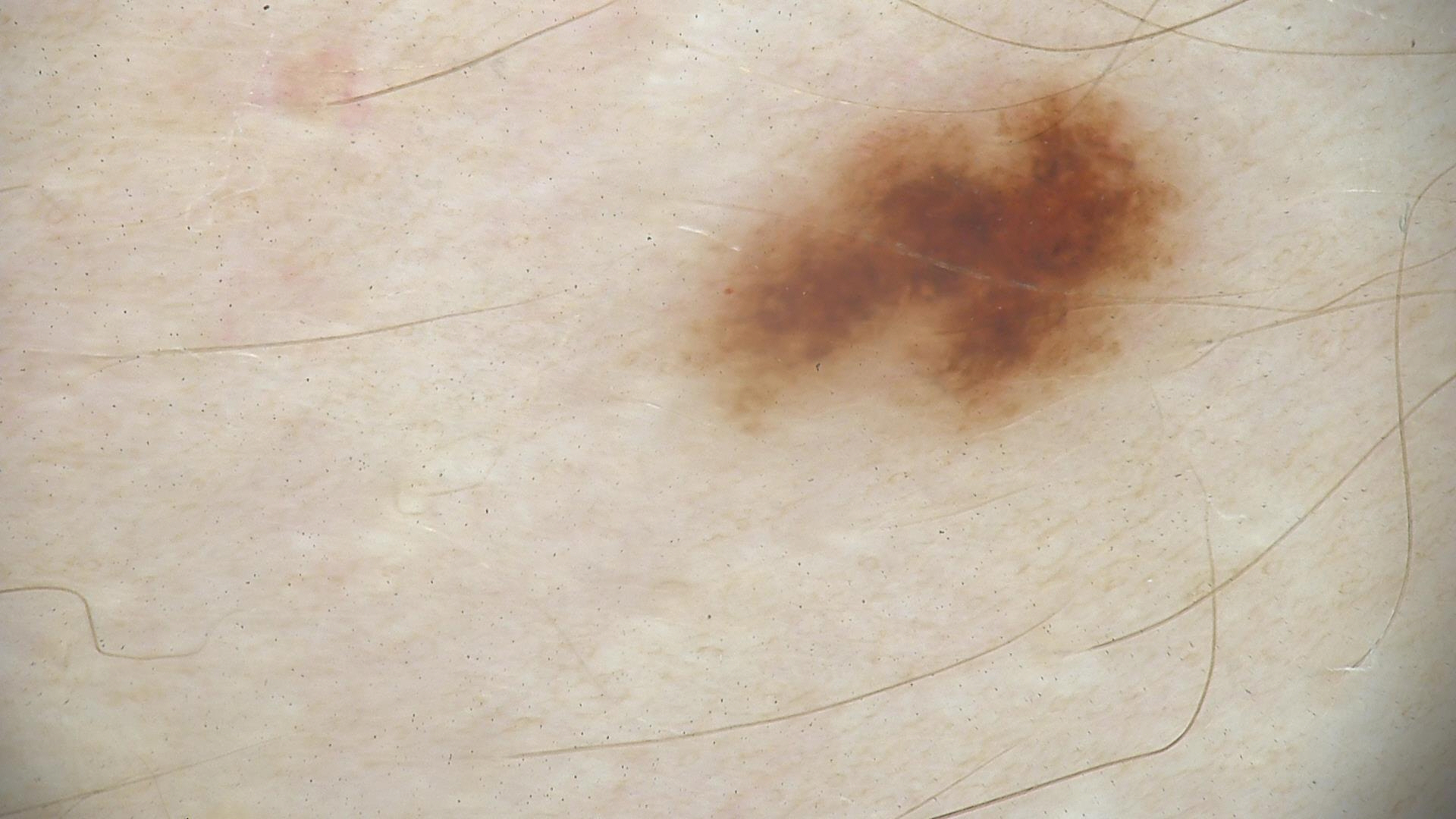  diagnosis:
    name: dysplastic junctional nevus
    code: jd
    malignancy: benign
    super_class: melanocytic
    confirmation: expert consensus